The patient says their skin reddens with sun exposure · collected as part of a research study, without a referral diagnosis · a male subject 73 years old · on a questionnaire the patient reported a personal history of cancer · numerous moles by the patient's own estimate:
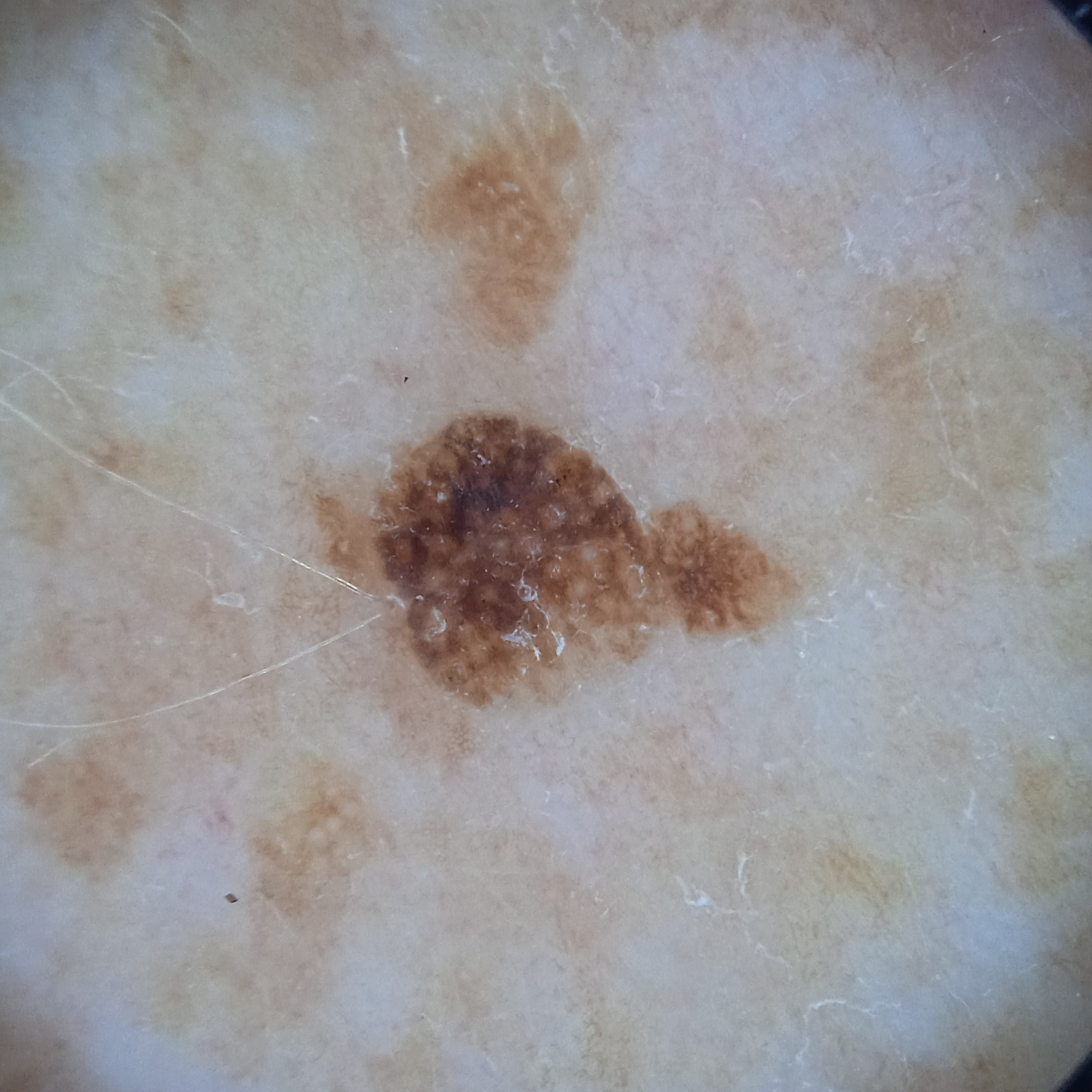Located on the back. The lesion measures approximately 5.5 mm. The dermatologists' assessment was a seborrheic keratosis.